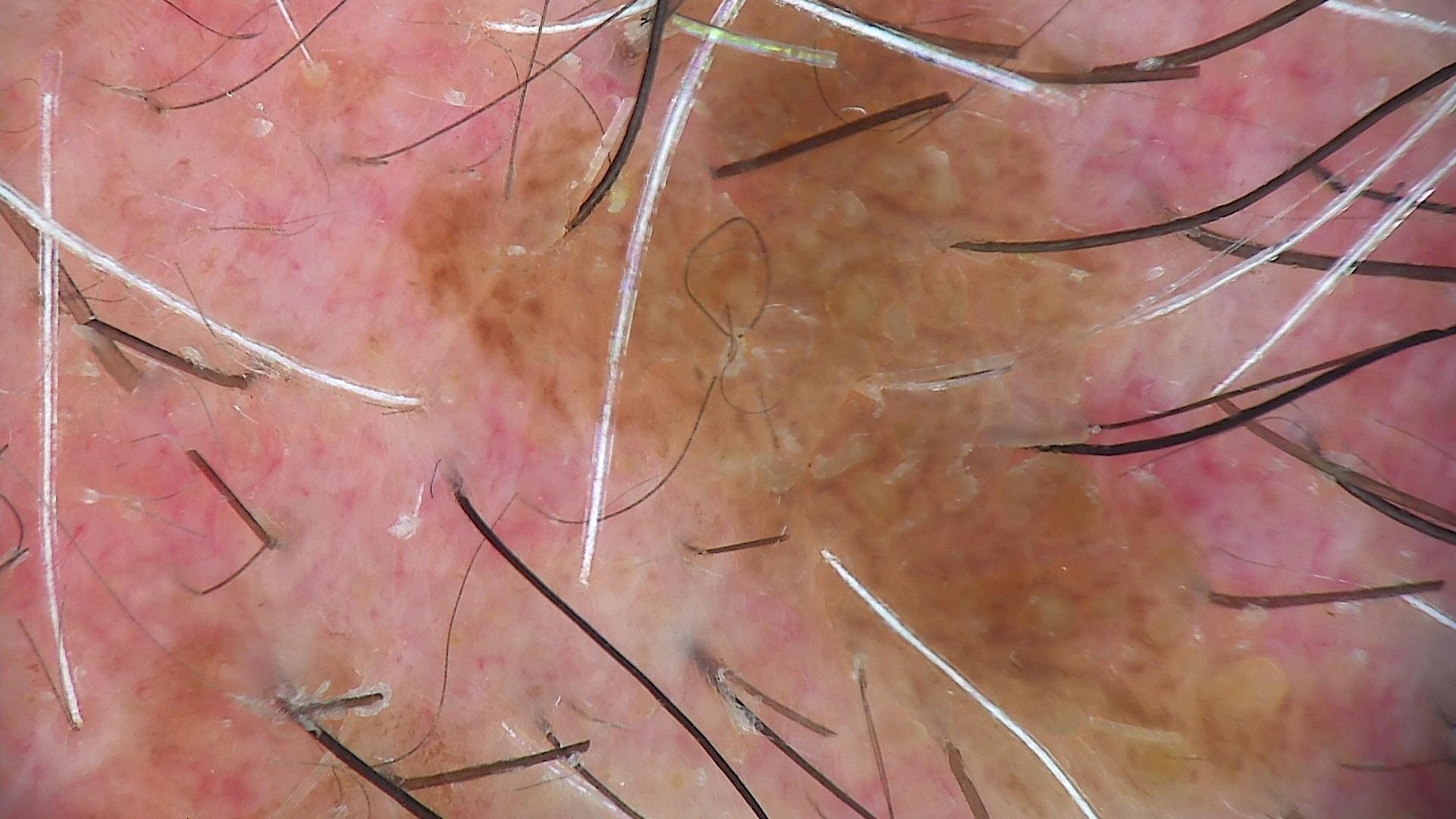Dermoscopy of a skin lesion.
The diagnostic label was a keratinocytic, benign lesion — a seborrheic keratosis.